The photo was captured at a distance; present for three to twelve months; the contributor reports the lesion is flat and rough or flaky; the patient described the issue as a rash; symptoms reported: bothersome appearance, itching and enlargement — 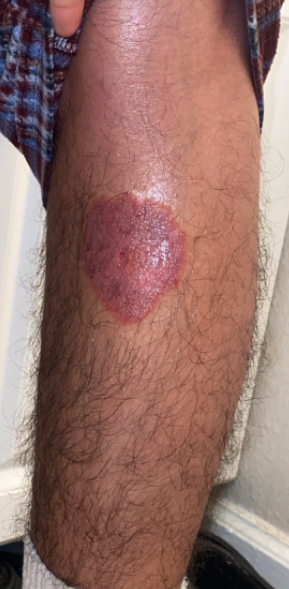The case was difficult to assess from the available photograph.